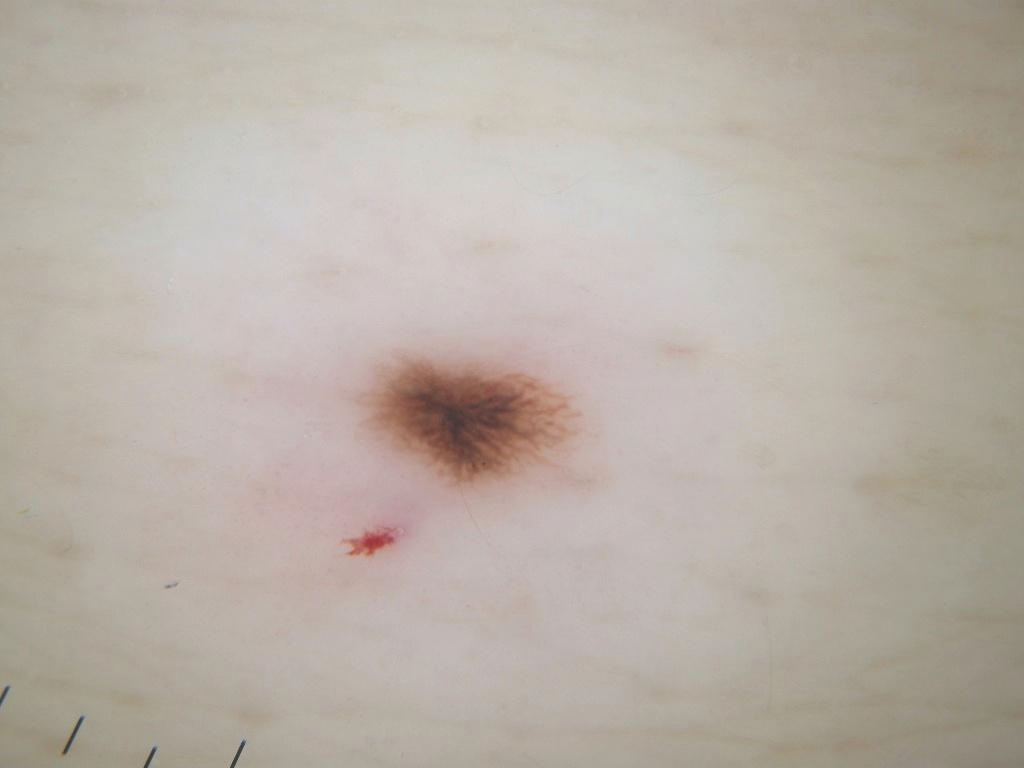A dermoscopic view of a skin lesion.
A female patient aged 48 to 52.
With coordinates (x1, y1, x2, y2), lesion location: box(349, 347, 604, 503).
A small lesion occupying a minor part of the field.
Dermoscopy demonstrates pigment network.
The lesion was assessed as a melanocytic nevus, a benign skin lesion.